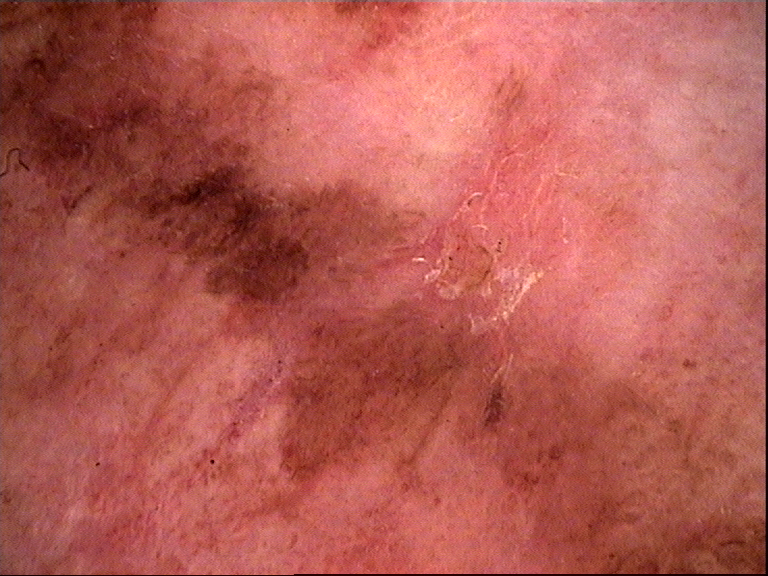Findings: A dermoscopic photograph of a skin lesion. This is a keratinocytic lesion. Pathology: The biopsy diagnosis was Bowen's disease.